The photograph is a close-up of the affected area · Fitzpatrick phototype II; non-clinician graders estimated MST 2 (US pool) or 3 (India pool) · the condition has been present for about one day · the patient described the issue as skin that appeared healthy to them · the lesion is described as rough or flaky · the patient did not report lesion symptoms · the subject is a female aged 60–69 · the lesion involves the back of the hand.
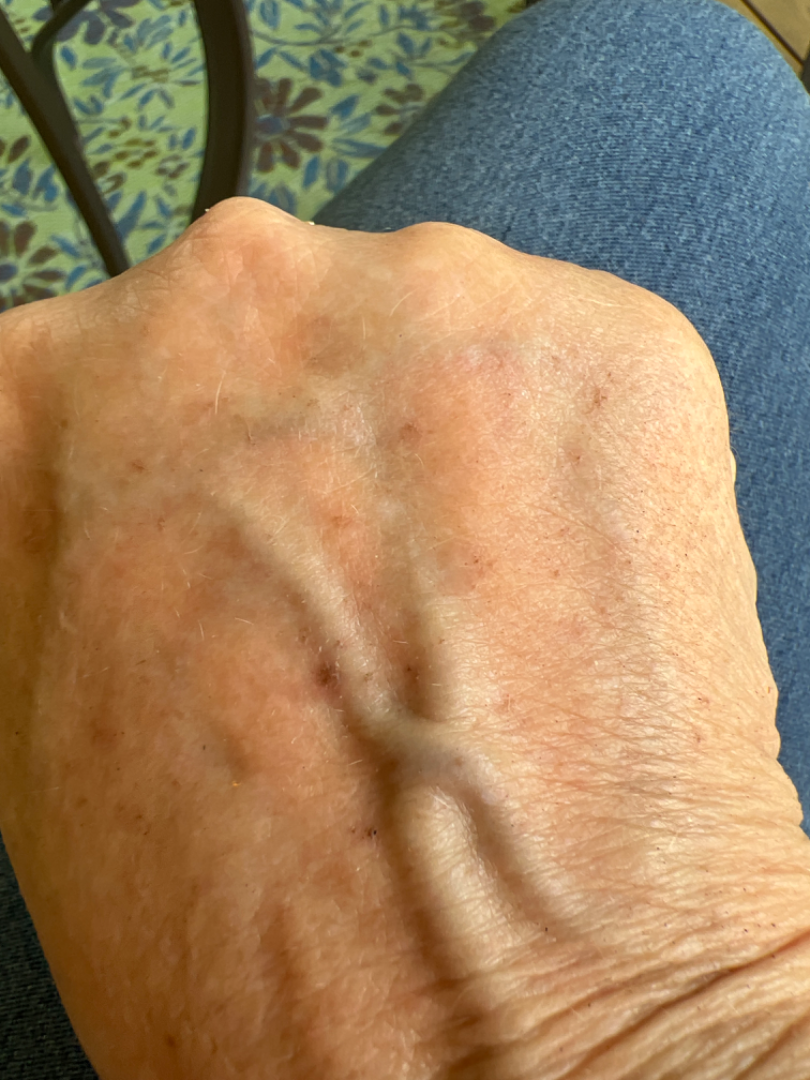differential diagnosis = in keeping with Actinic Keratosis.